This image was taken at an angle. Female contributor, age 18–29. The arm is involved:
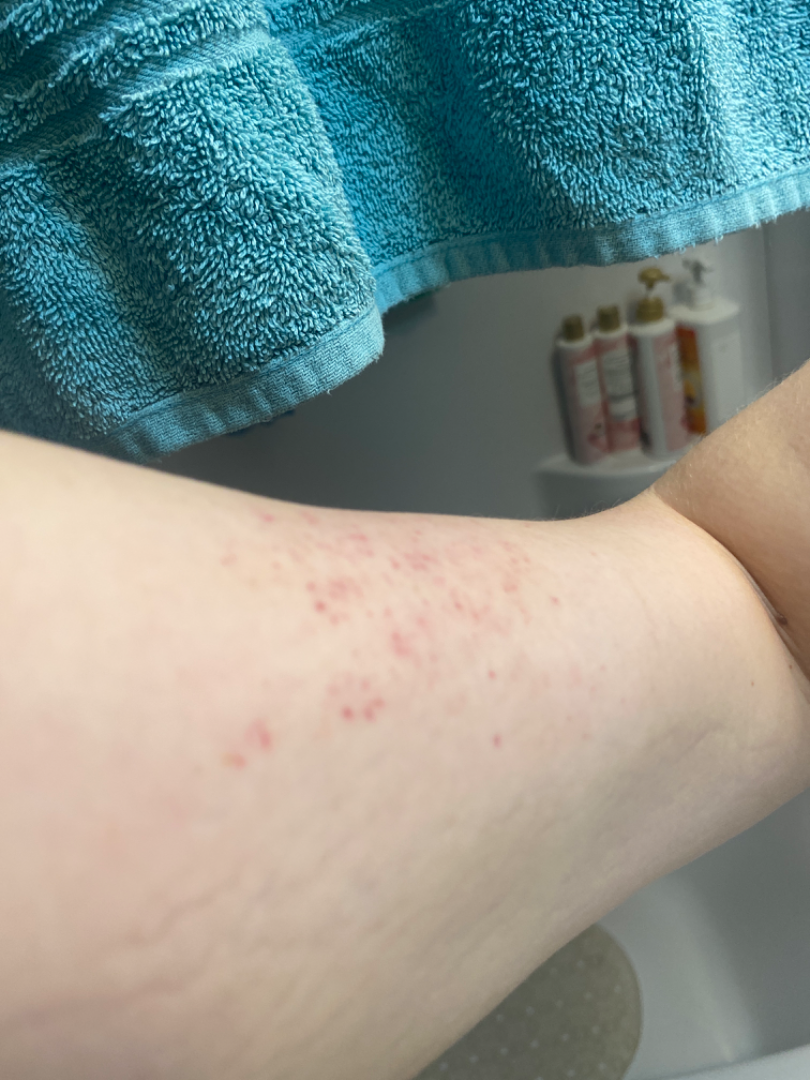Favoring petechiae.